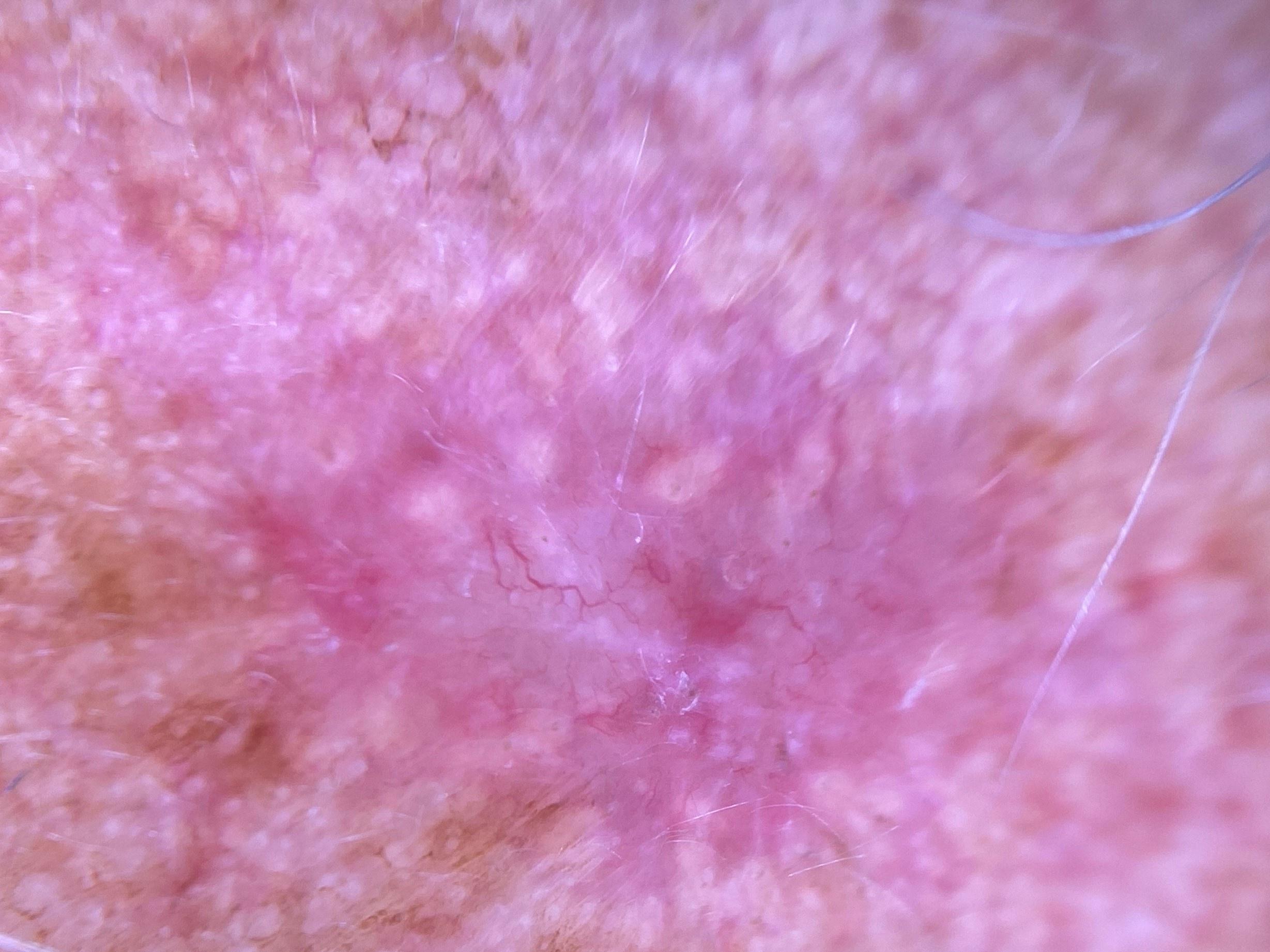| field | value |
|---|---|
| relevant background | no prior melanoma and no first-degree relative with melanoma |
| subject | male, in their 70s |
| Fitzpatrick | III |
| image type | dermoscopic image |
| site | the head or neck |
| diagnostic label | Basal cell carcinoma (biopsy-proven) |